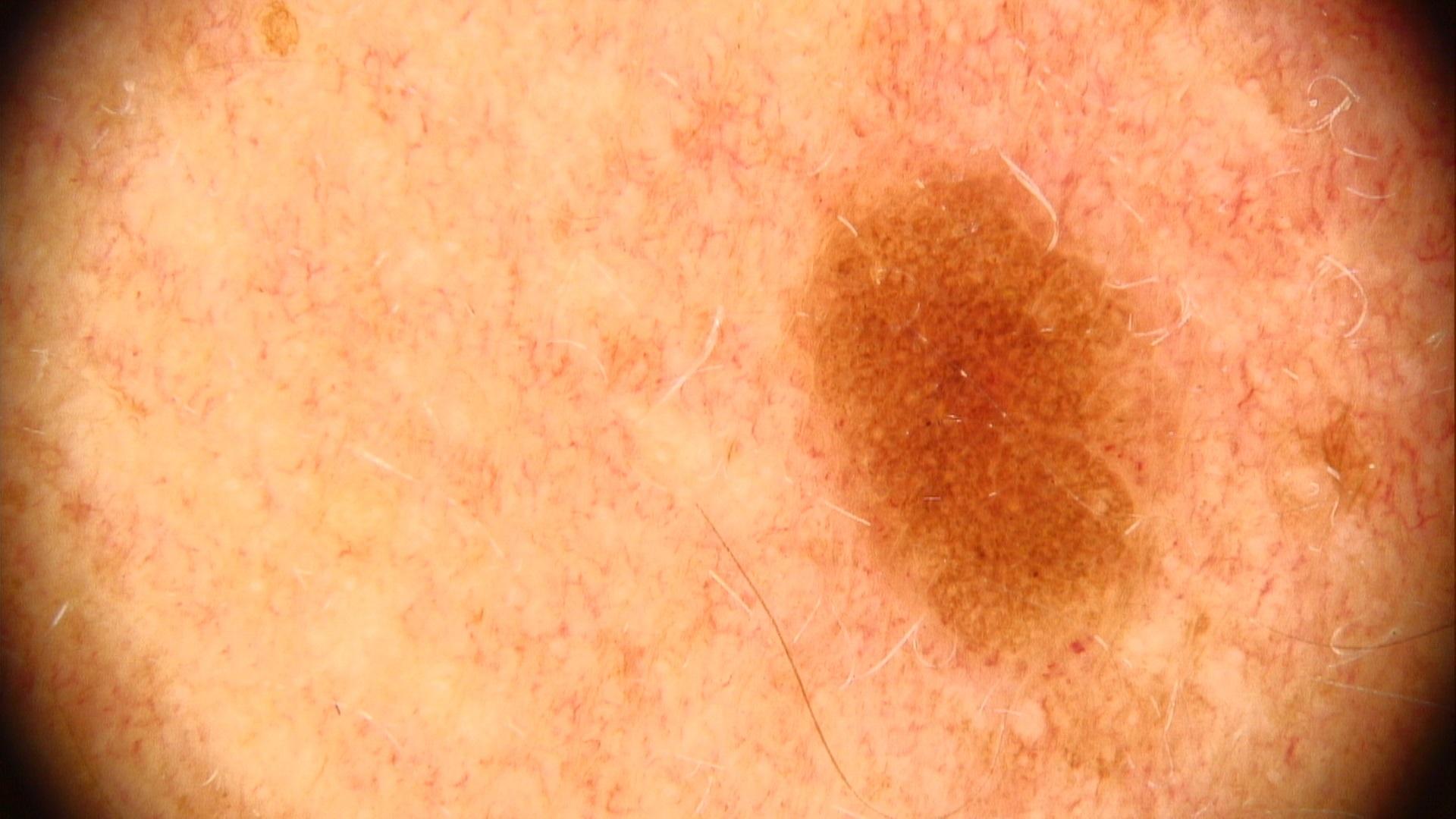Clinical context: A male patient aged around 40. A dermoscopic photograph of a skin lesion. The chart notes melanoma in a first-degree relative. The patient was assessed as skin type III. Located on the head or neck. Assessment: Expert review favored a benign lesion — a nevus.